A clinical photograph of a skin lesion.
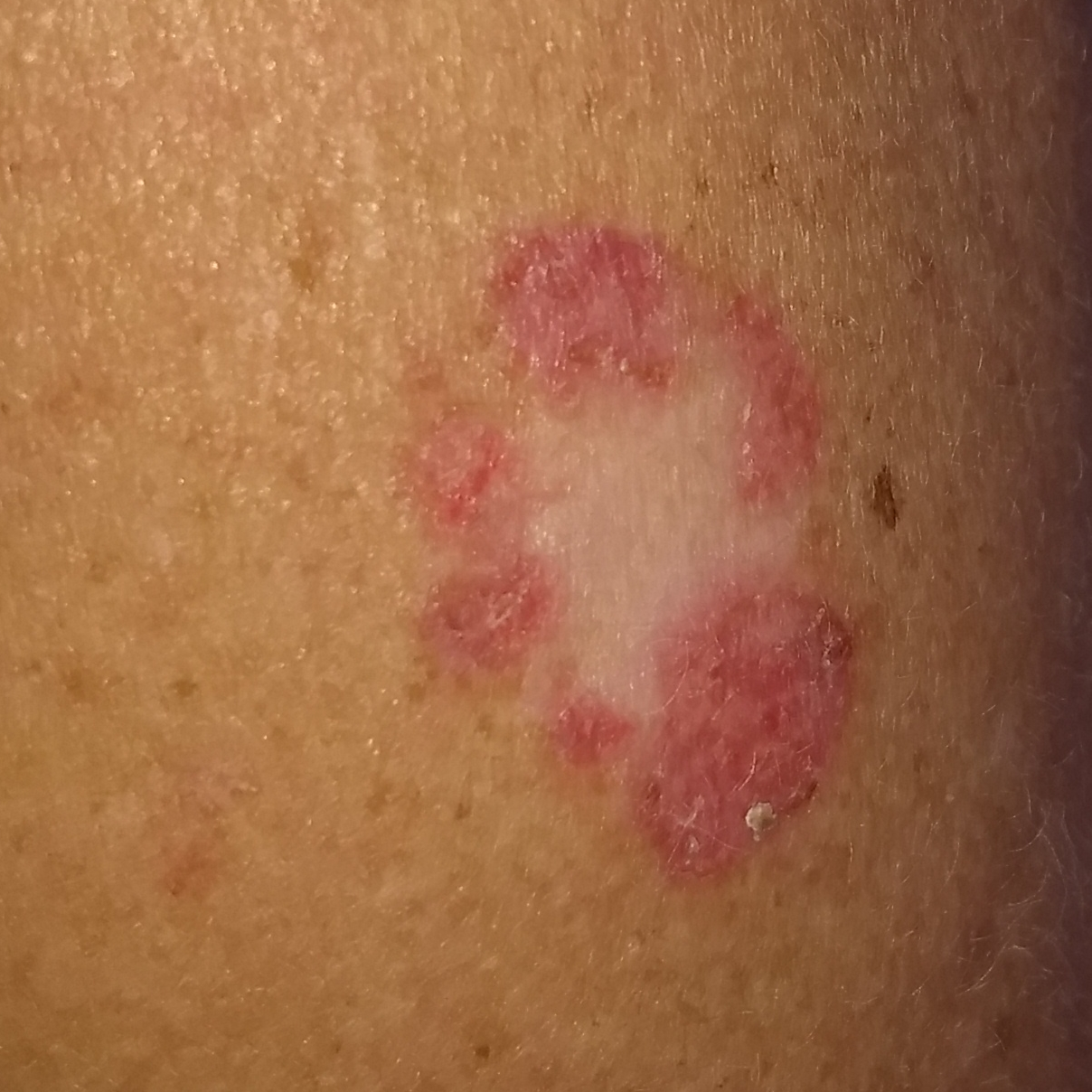location: the chest | diagnosis: basal cell carcinoma (biopsy-proven).